A skin lesion imaged with a dermatoscope.
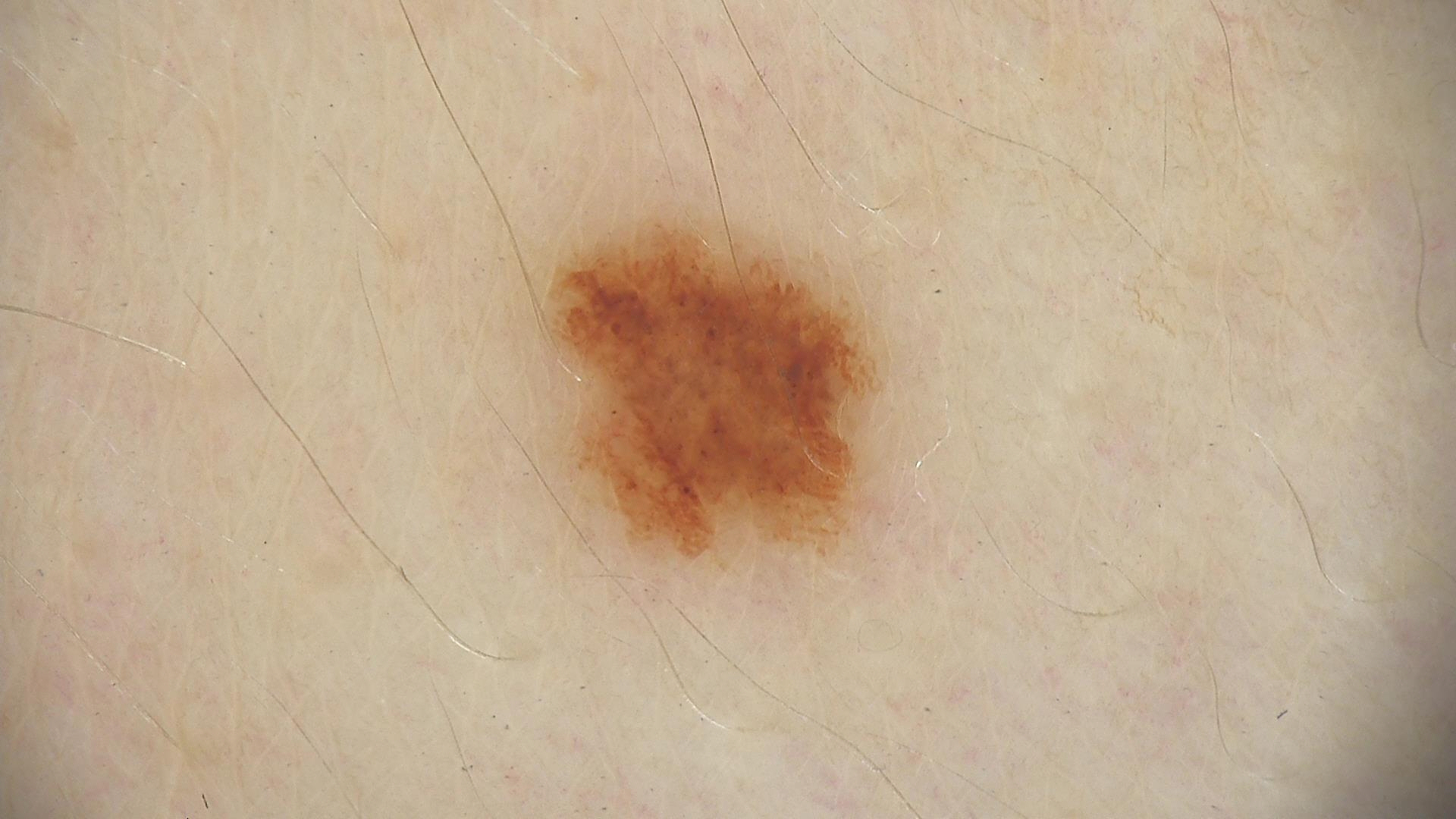diagnosis: dysplastic junctional nevus (expert consensus).